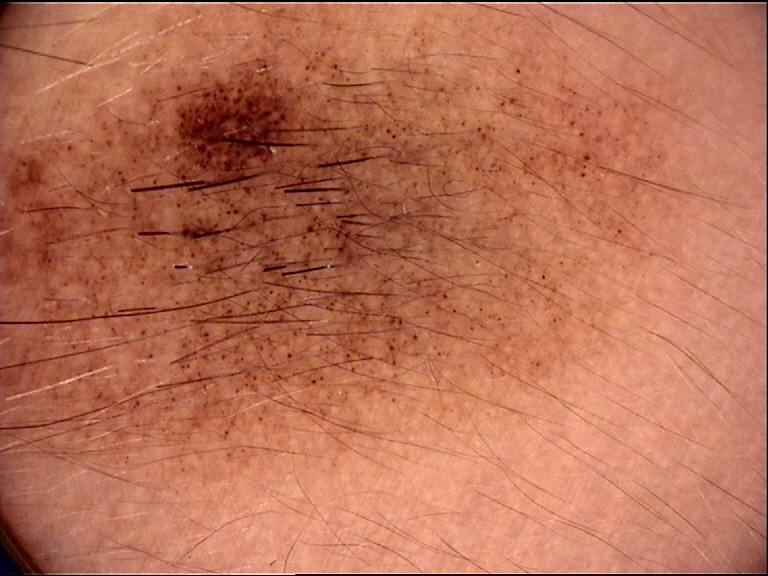assessment: congenital junctional nevus (expert consensus).